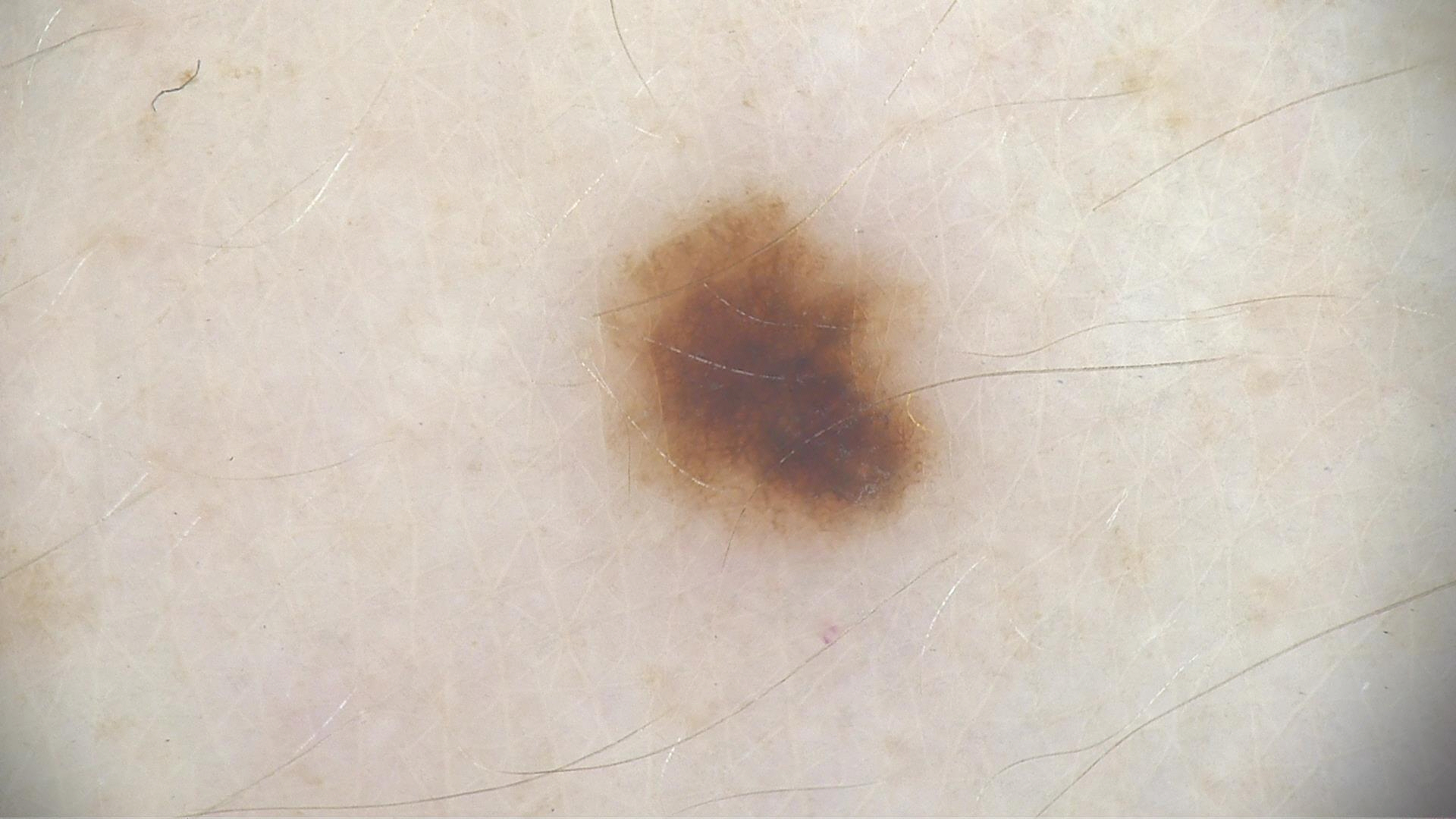A skin lesion imaged with a dermatoscope.
Labeled as a dysplastic junctional nevus.